The photograph was taken at a distance: 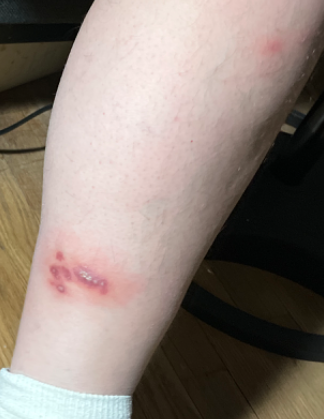On remote dermatologist review: the leading consideration is Insect Bite; possibly Pyoderma Gangrenosum; also raised was purulent pustules.